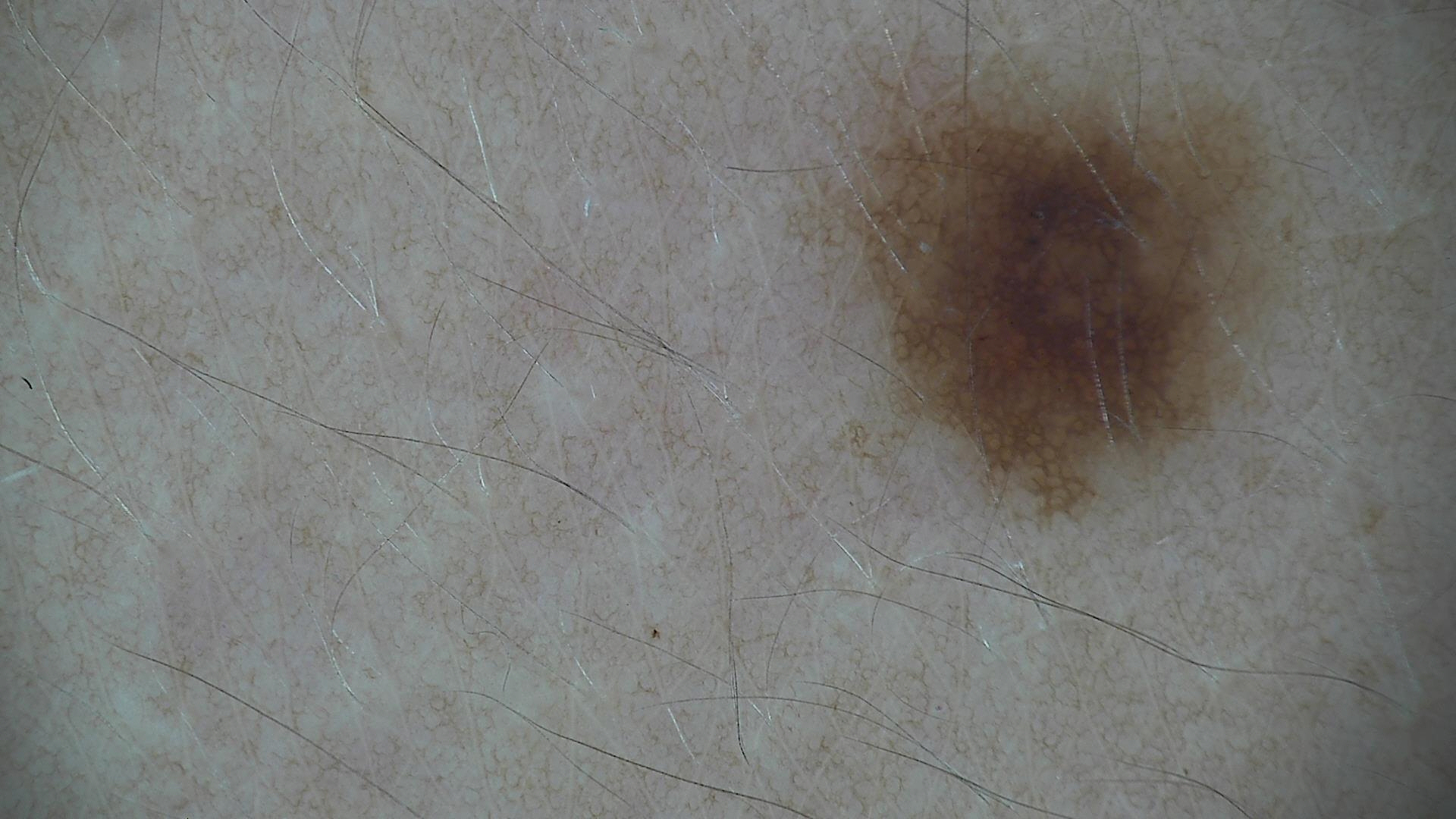<lesion>
<image>dermatoscopy</image>
<diagnosis>
<name>dysplastic junctional nevus</name>
<code>jd</code>
<malignancy>benign</malignancy>
<super_class>melanocytic</super_class>
<confirmation>expert consensus</confirmation>
</diagnosis>
</lesion>